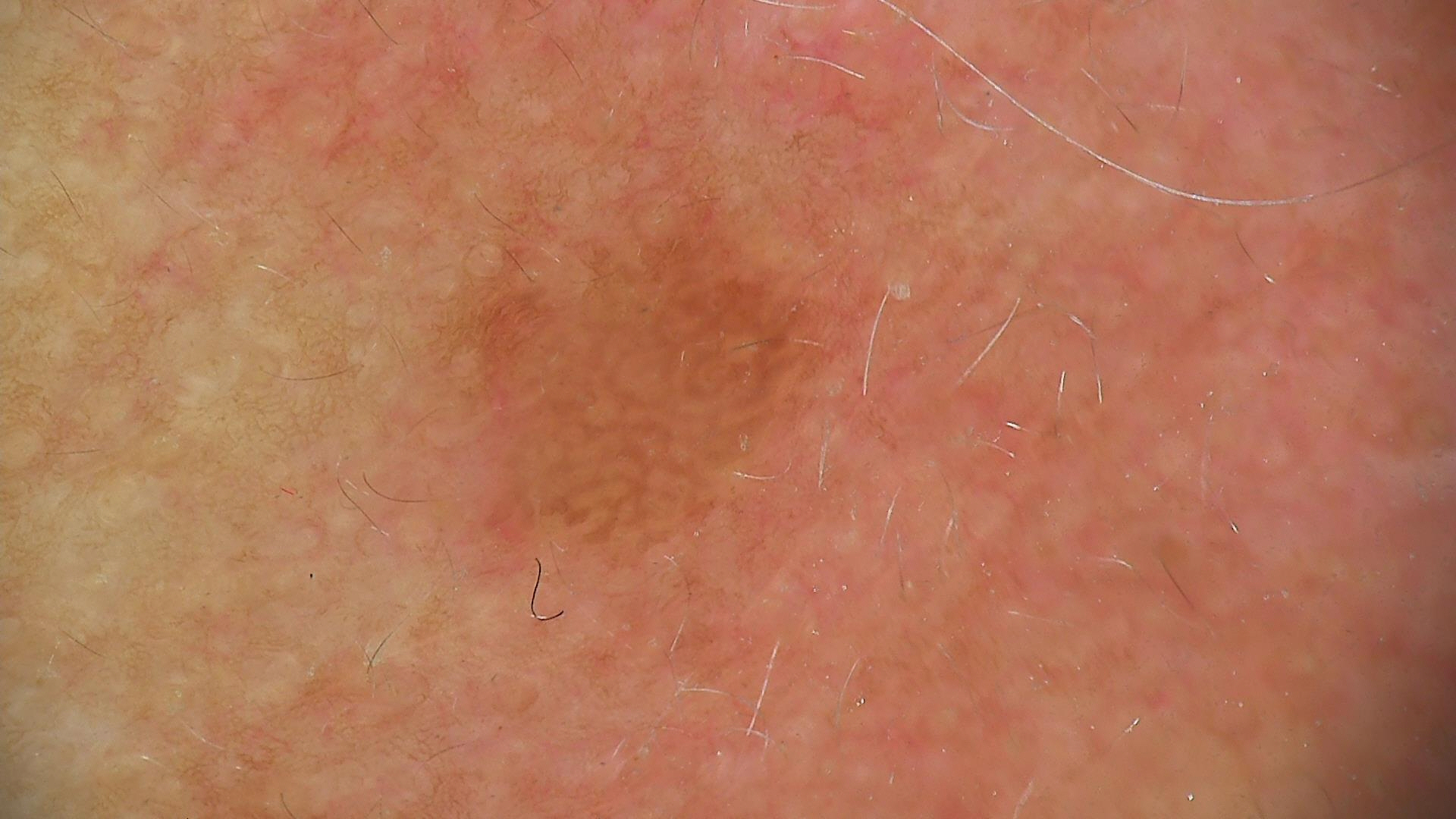classification: keratinocytic; label: seborrheic keratosis (expert consensus).